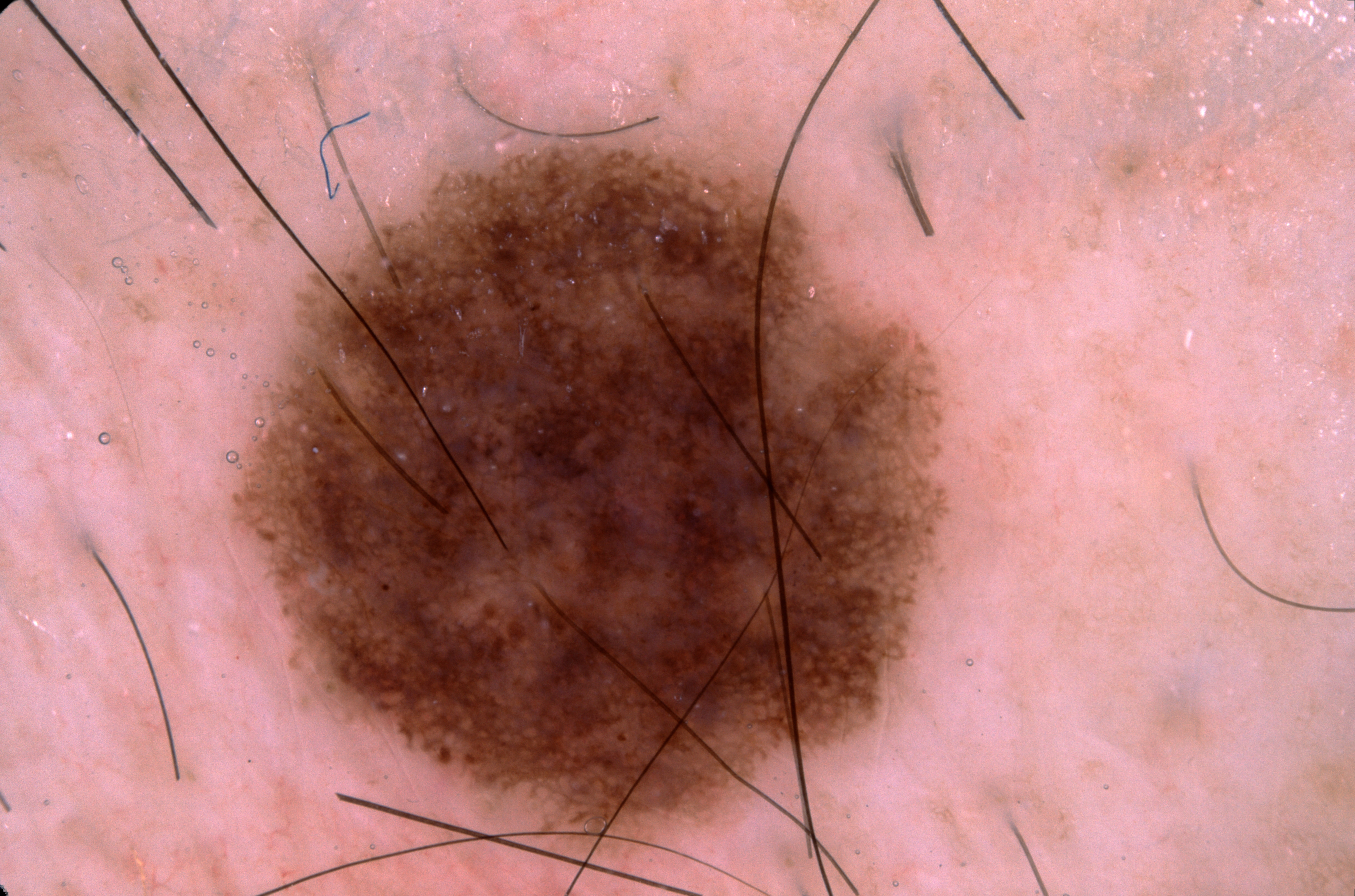imaging = dermatoscopic image of a skin lesion | subject = male, aged approximately 65 | location = x1=233, y1=140, x2=953, y2=861 | dermoscopic features = pigment network and milia-like cysts; absent: streaks and negative network | extent = large | assessment = a melanocytic nevus, a benign lesion.